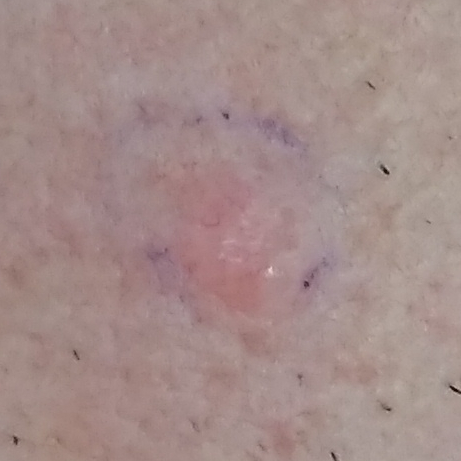Histopathology confirmed a basal cell carcinoma.